Associated systemic symptoms include fatigue and joint pain. The patient reports enlargement, bothersome appearance and darkening. The head or neck, back of the torso and front of the torso are involved. The photograph was taken at a distance. Texture is reported as raised or bumpy and fluid-filled. The patient considered this a rash. Skin tone: FST II: 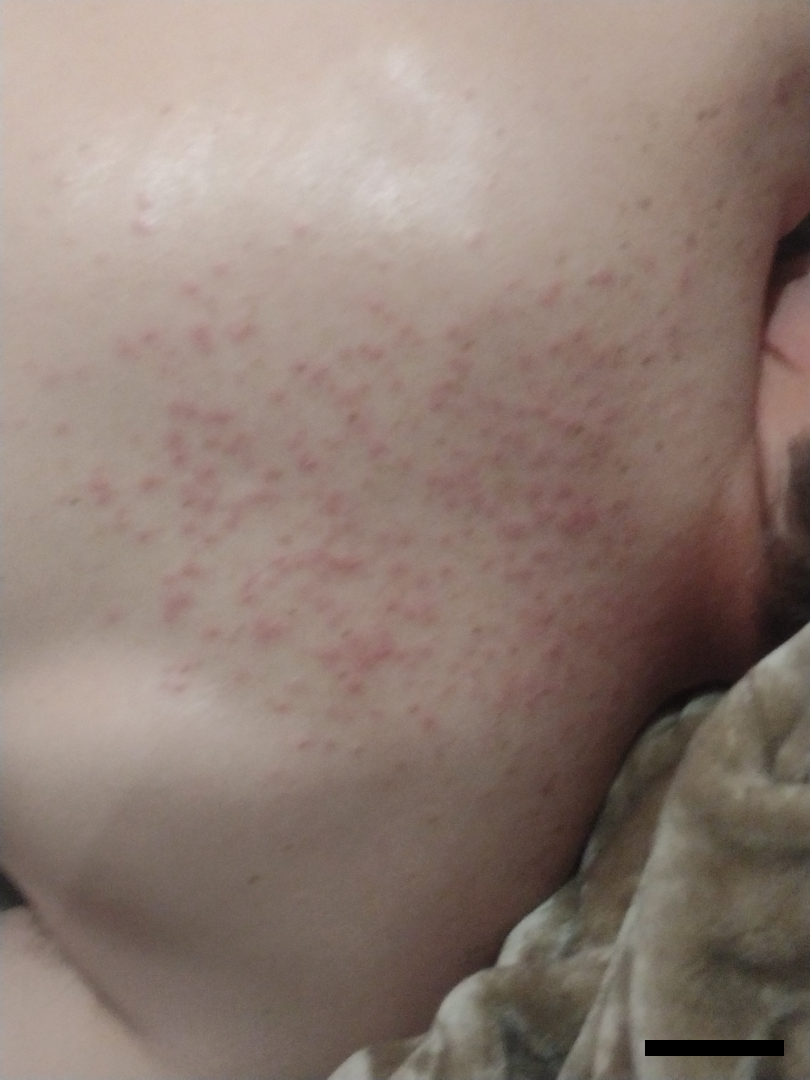A single dermatologist reviewed the case: the favored diagnosis is Folliculitis; also on the differential is Miliaria.